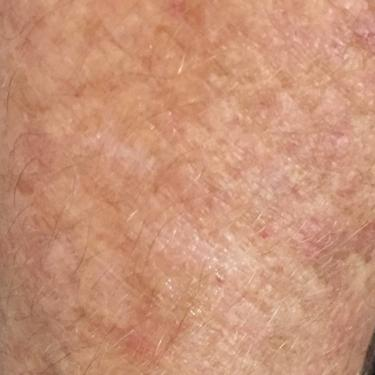A subject 65 years of age. The lesion is located on a forearm. The patient reports that the lesion itches. The consensus clinical diagnosis was a lesion of indeterminate malignant potential — an actinic keratosis.